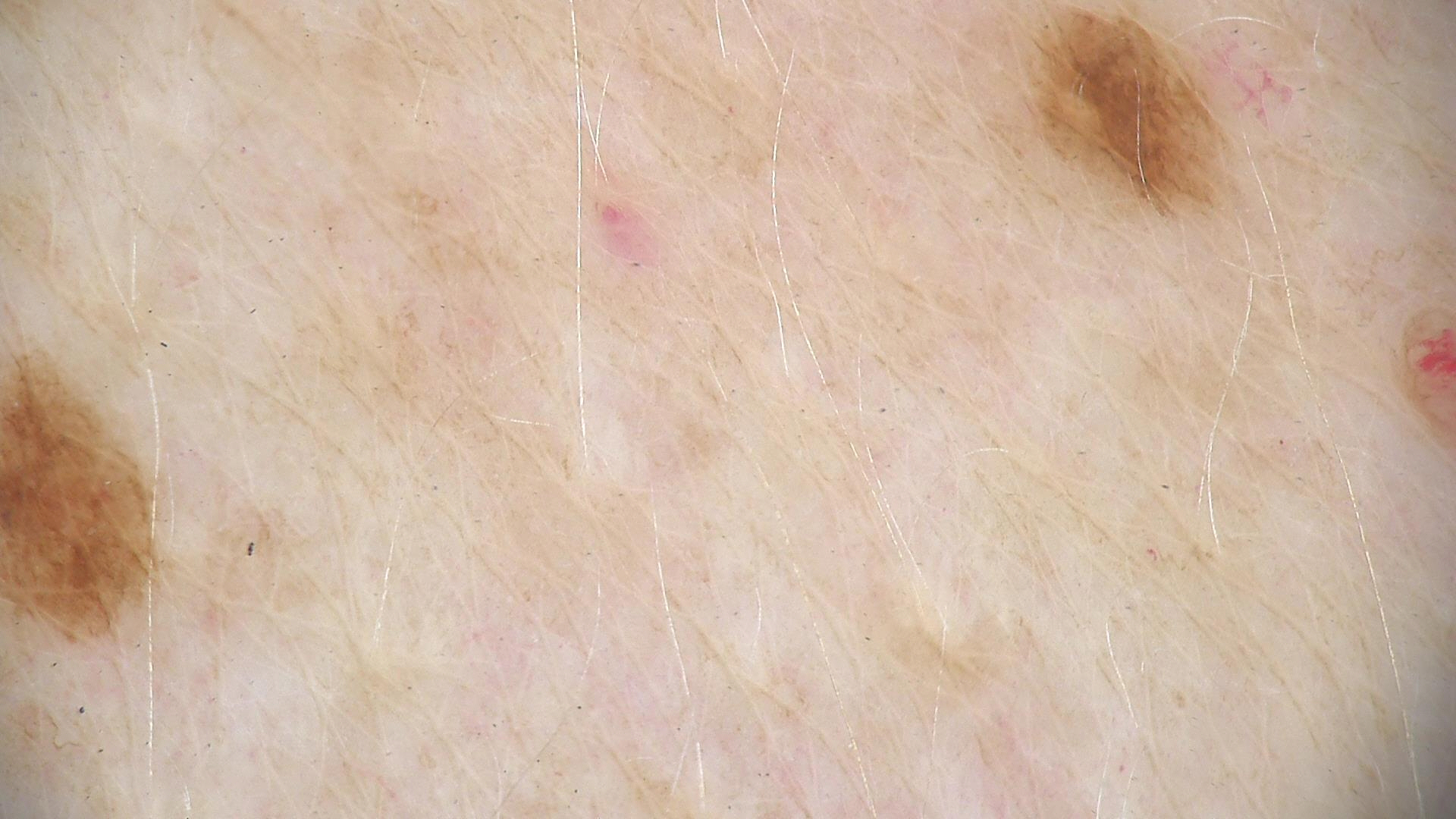class — dysplastic junctional nevus (expert consensus)